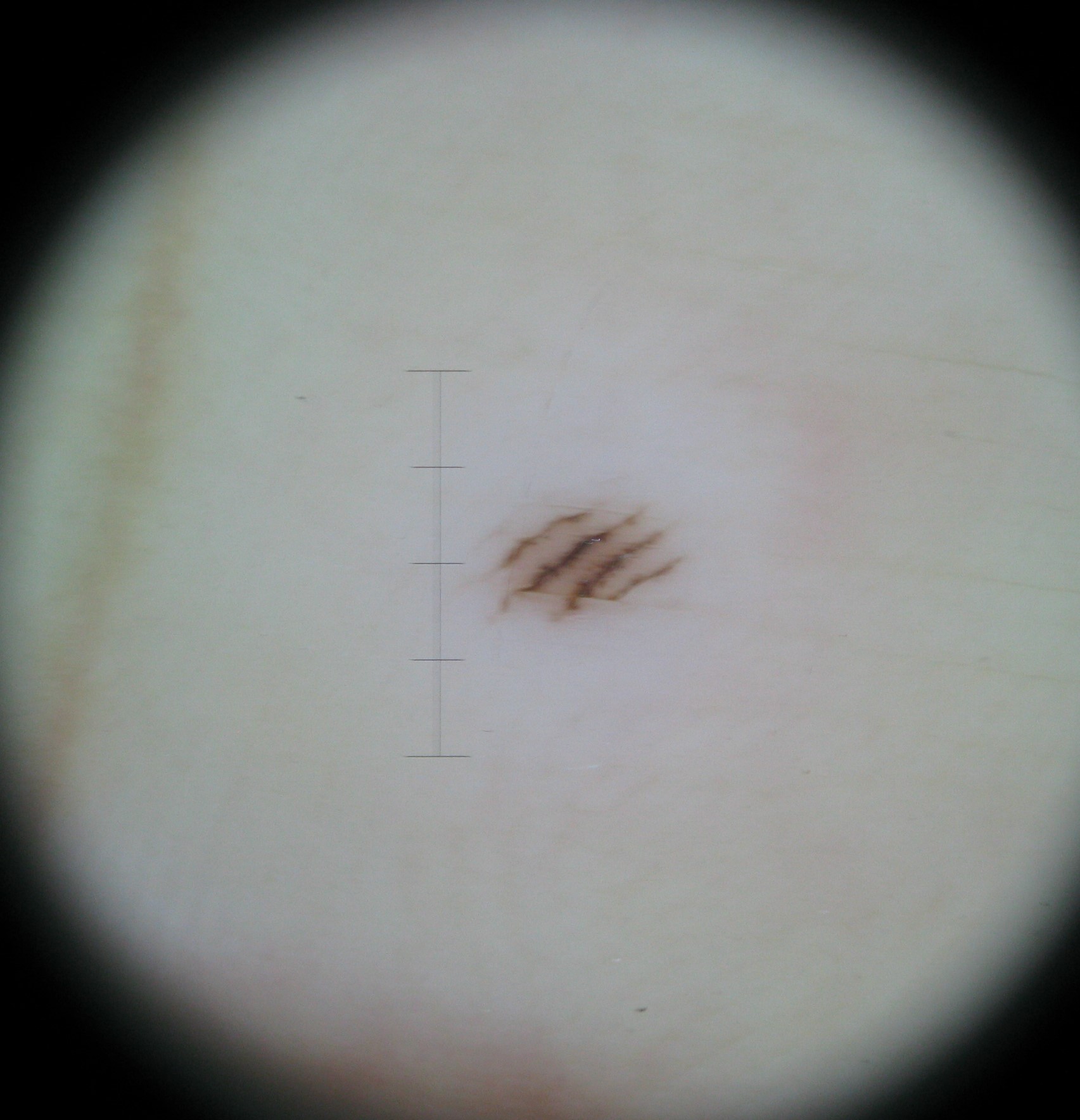A dermoscopy image of a single skin lesion. The architecture is that of a banal lesion. Diagnosed as an acral junctional nevus.